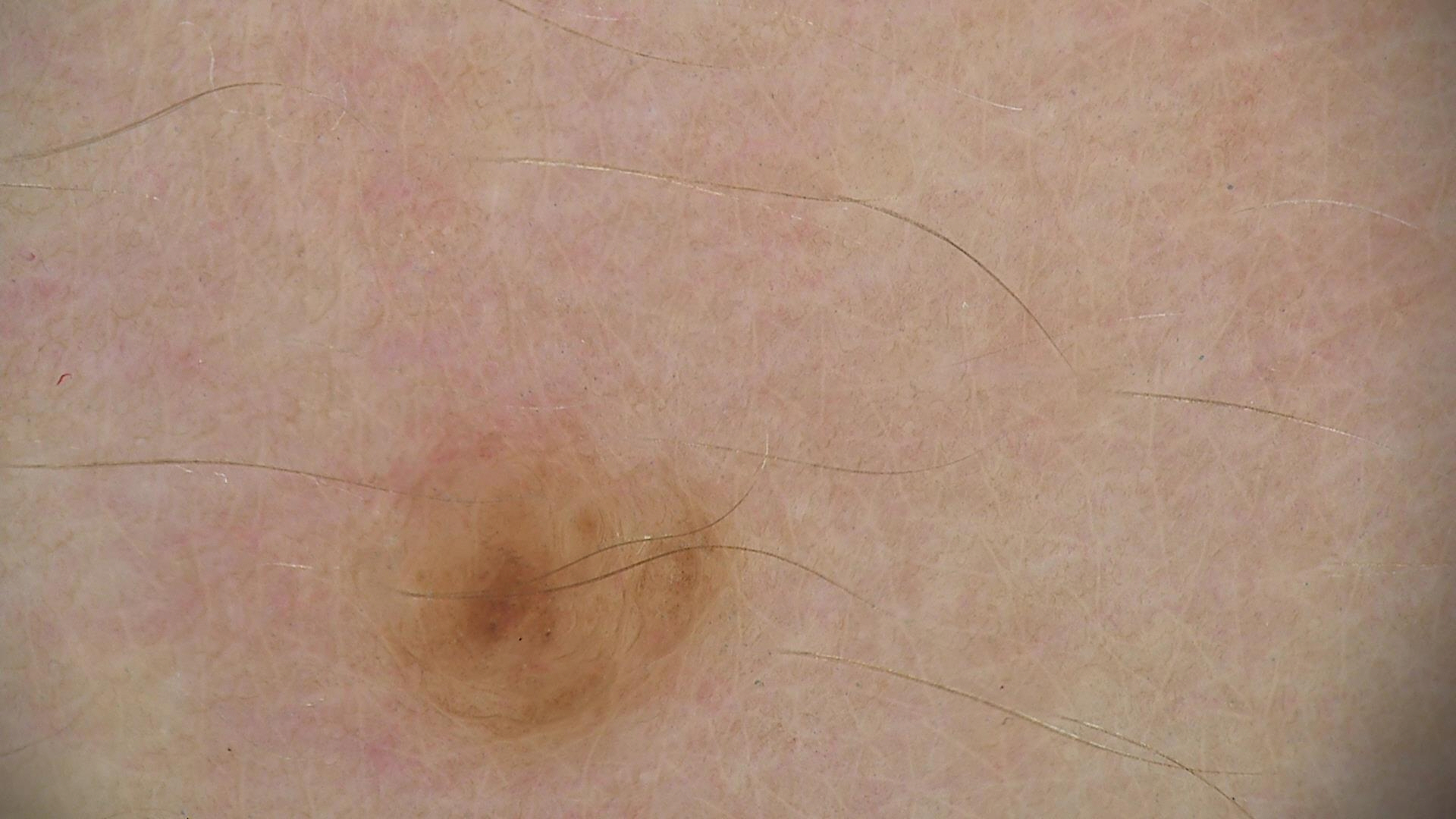The diagnosis was a dermal nevus.